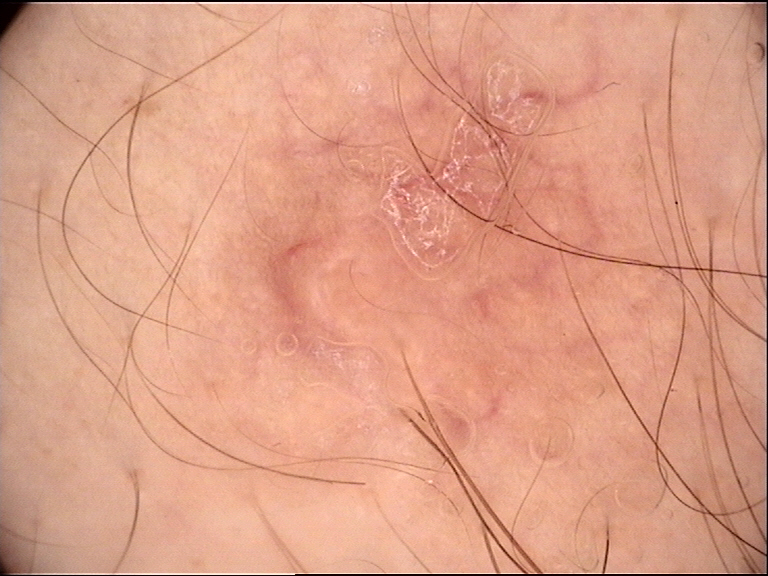A dermoscopic photograph of a skin lesion.
The diagnostic label was a banal lesion — a dermal nevus.